Close-up view: 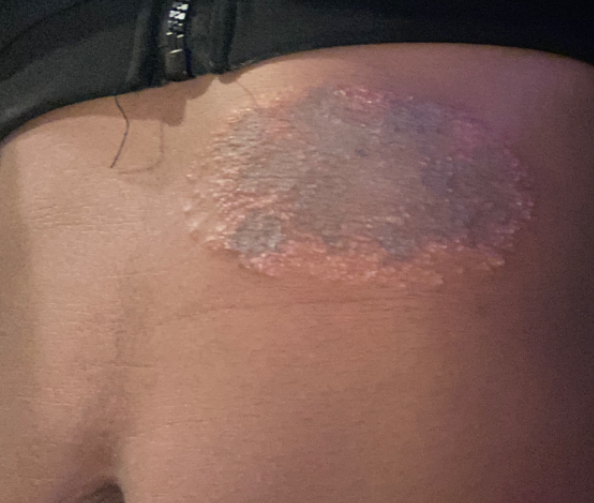On photographic review by a dermatologist: Fungal dermatitis, Cutaneous T Cell Lymphoma and Psoriasis were each considered, in no particular order.